No relevant systemic symptoms, this image was taken at a distance, texture is reported as rough or flaky and raised or bumpy, reported lesion symptoms include itching and enlargement, Fitzpatrick skin type I, the affected area is the sole of the foot and leg:
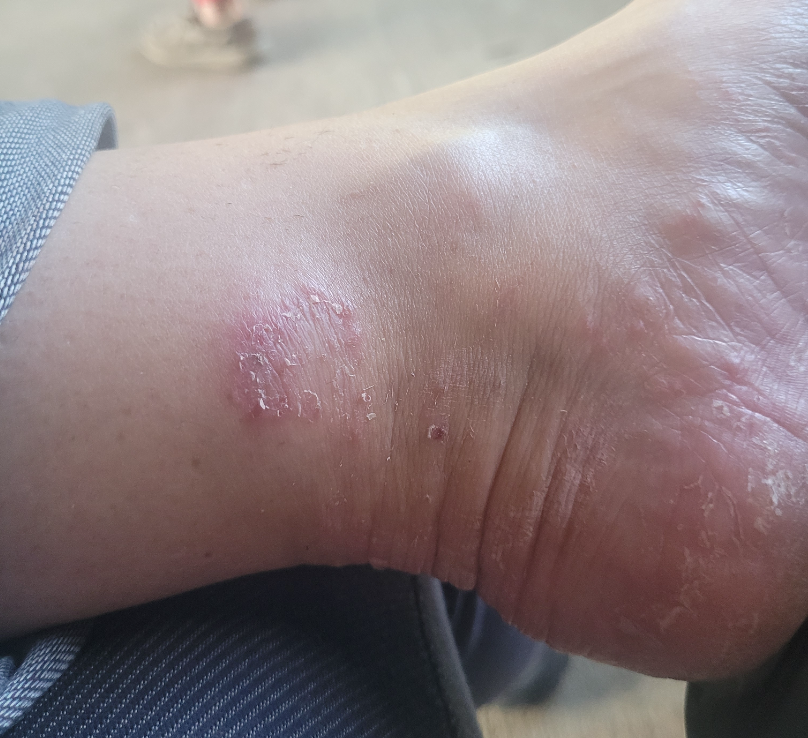{
  "differential": {
    "leading": [
      "Tinea"
    ],
    "considered": [
      "Psoriasis"
    ],
    "unlikely": [
      "Eczema"
    ]
  }
}